A dermoscopy image of a single skin lesion; the subject is a female about 40 years old — 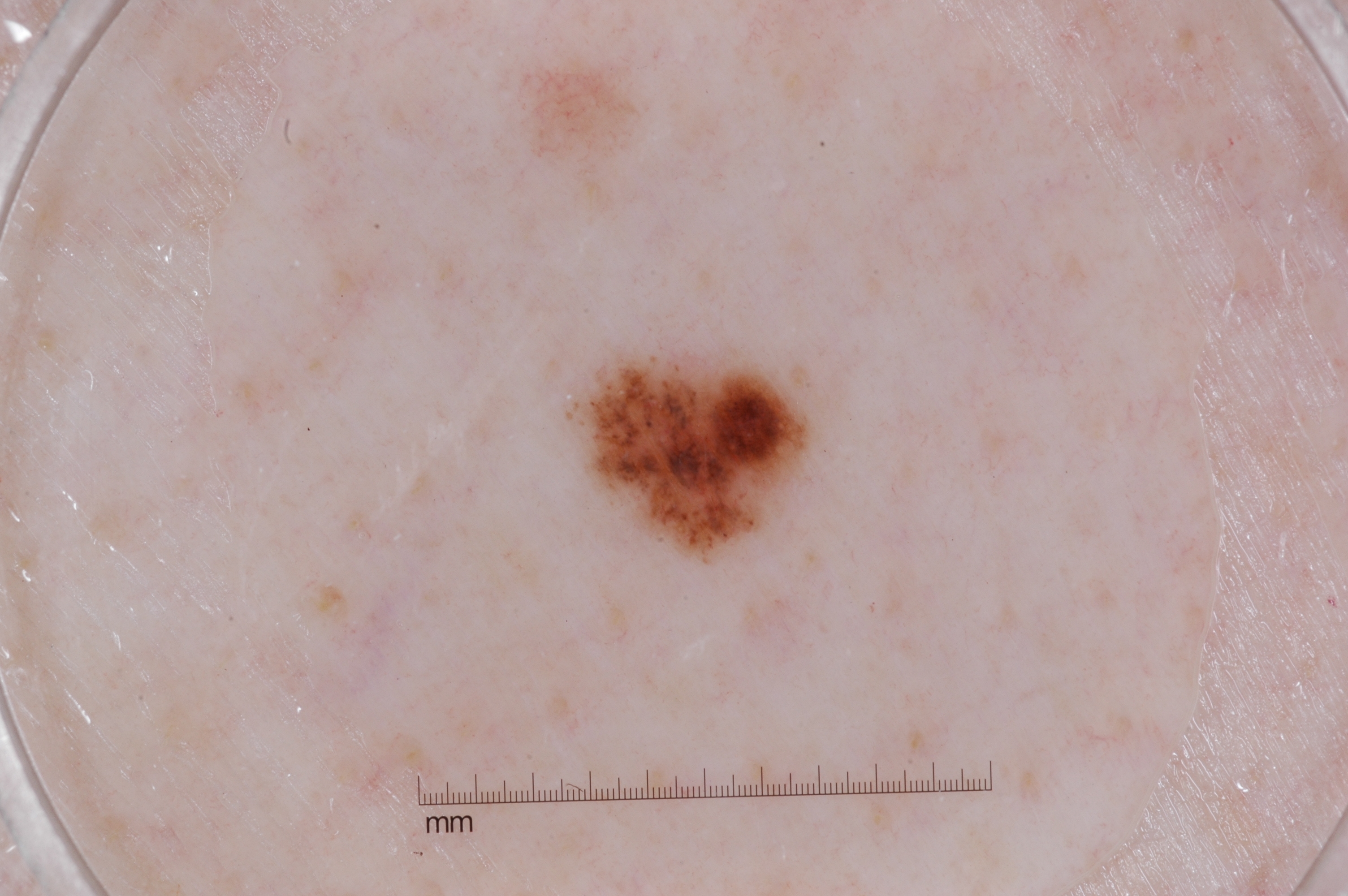| key | value |
|---|---|
| location | bbox(562, 339, 831, 567) |
| dermoscopic features not present | streaks, negative network, pigment network, and milia-like cysts |
| diagnostic label | a melanocytic nevus, a benign lesion |